Symptoms reported: bothersome appearance, enlargement and itching. Female contributor, age 18–29. A close-up photograph. No relevant systemic symptoms. The patient considered this a rash. The patient reports the condition has been present for less than one week. Located on the leg. The patient reports the lesion is raised or bumpy: 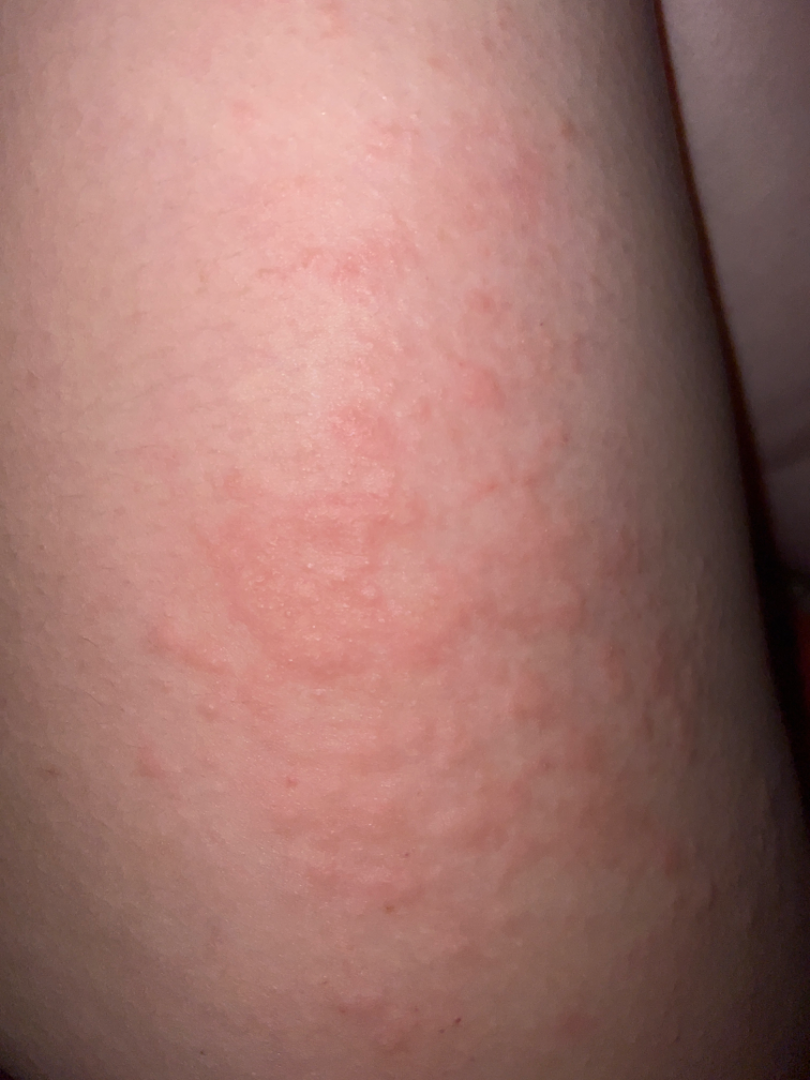On teledermatology review: the impression on review was Acute dermatitis, NOS.